A dermoscopic photograph of a skin lesion:
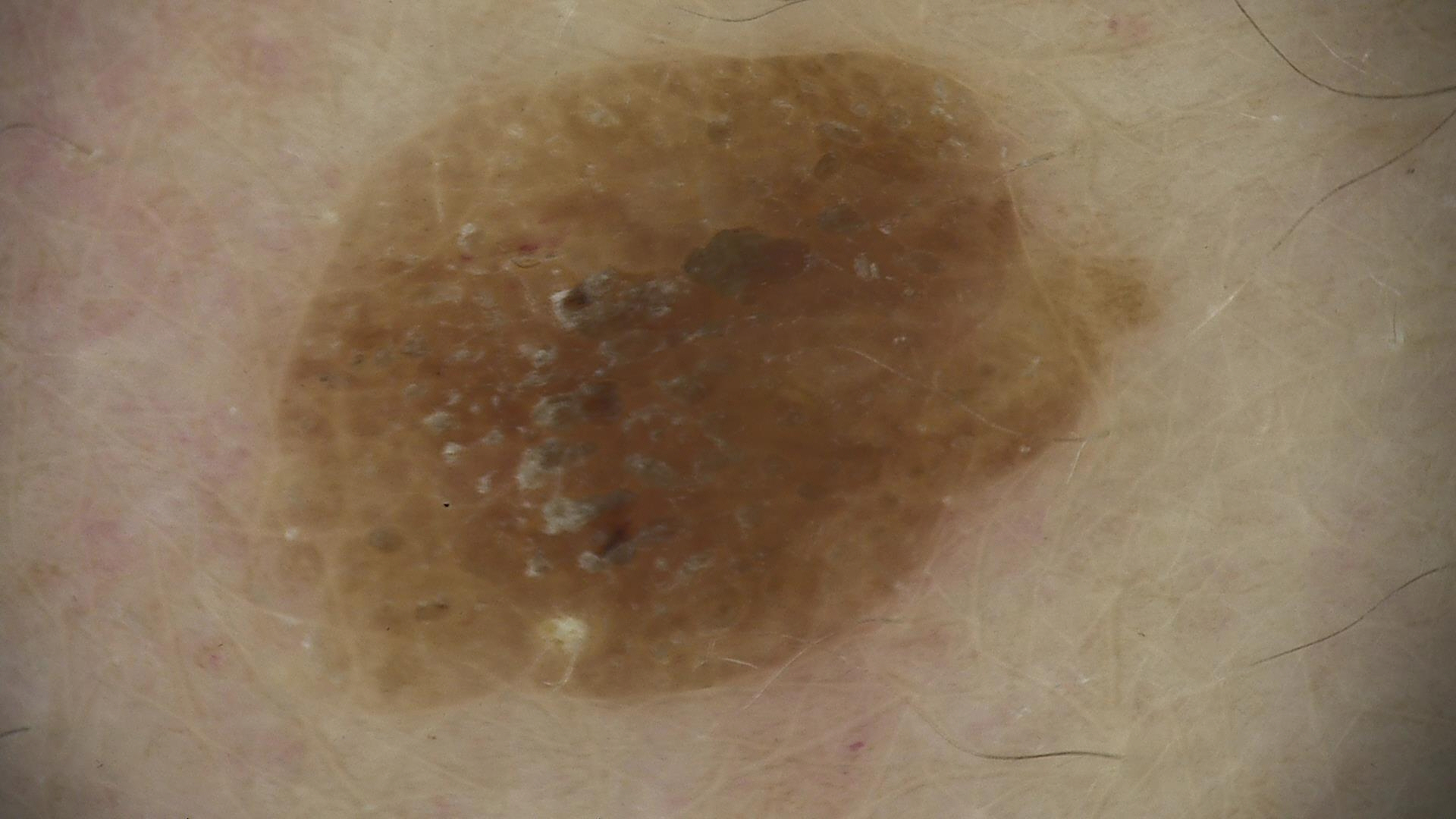{
  "lesion_type": {
    "main_class": "keratinocytic"
  },
  "diagnosis": {
    "name": "seborrheic keratosis",
    "code": "sk",
    "malignancy": "benign",
    "super_class": "non-melanocytic",
    "confirmation": "expert consensus"
  }
}